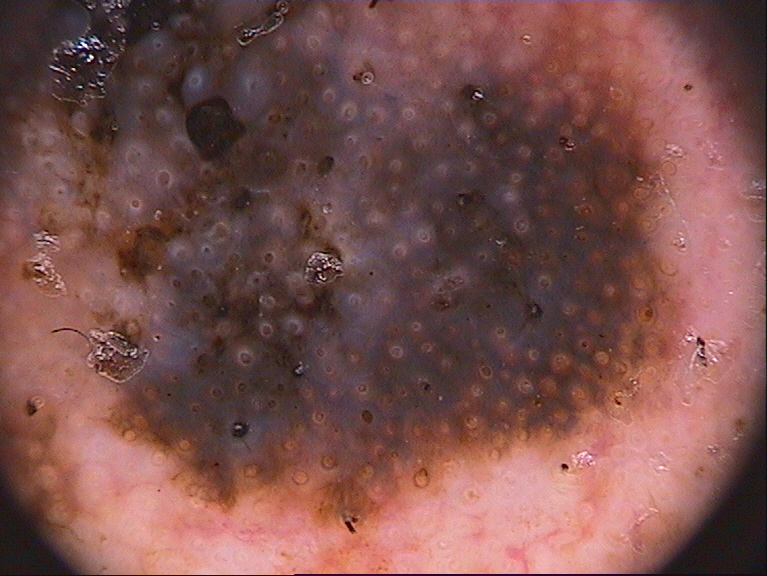Summary: A dermatoscopic image of a skin lesion. The visible lesion spans x1=1 y1=1 x2=695 y2=530. The dermoscopic pattern shows pigment network, with no streaks, milia-like cysts, globules, or negative network. Diagnosis: Confirmed on histopathology as a melanoma.